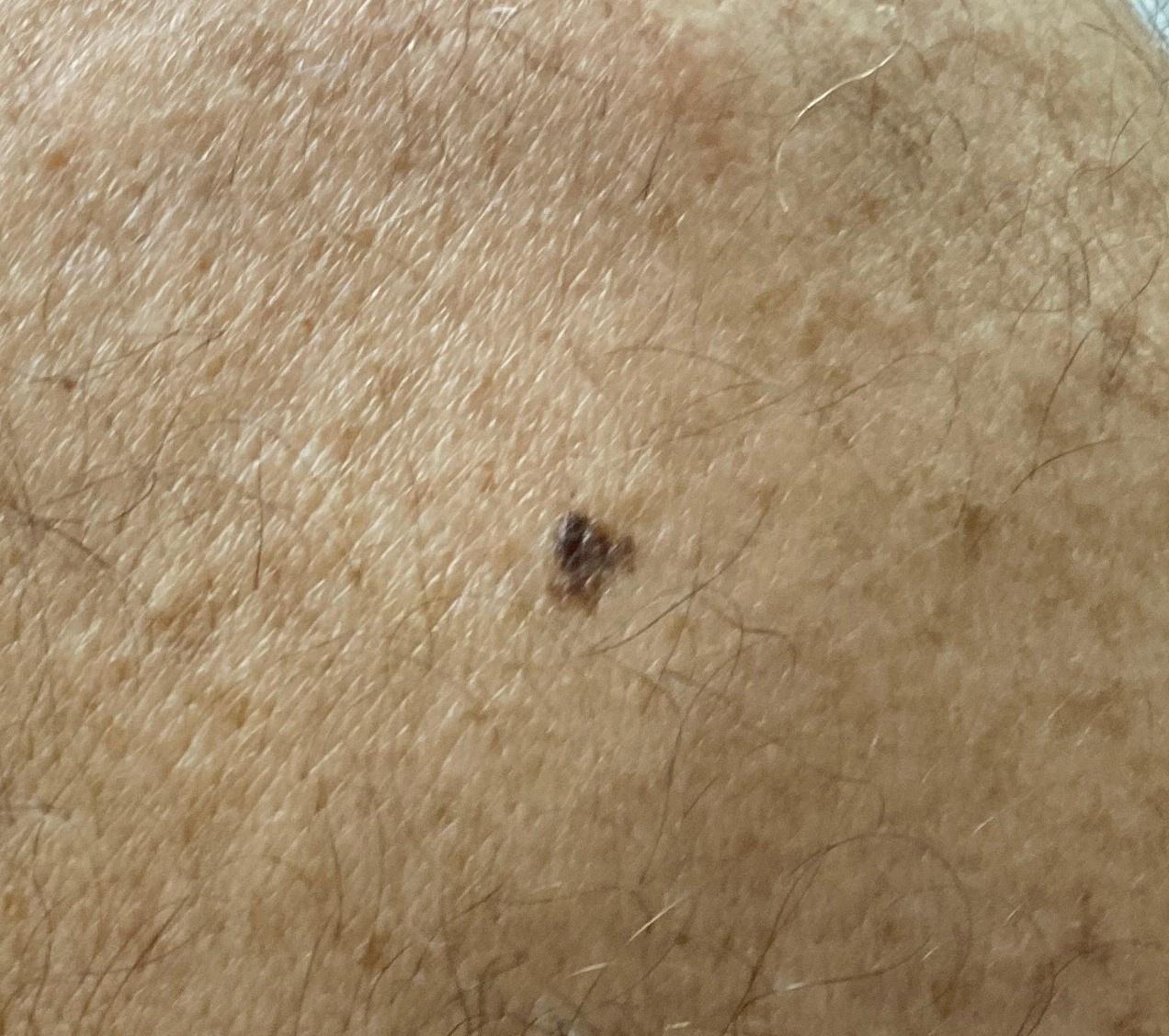relevant background = a previous melanoma | imaging = clinical photograph | patient = male, aged approximately 80 | body site = the trunk, specifically the posterior trunk | diagnostic label = Nevus (biopsy-proven).